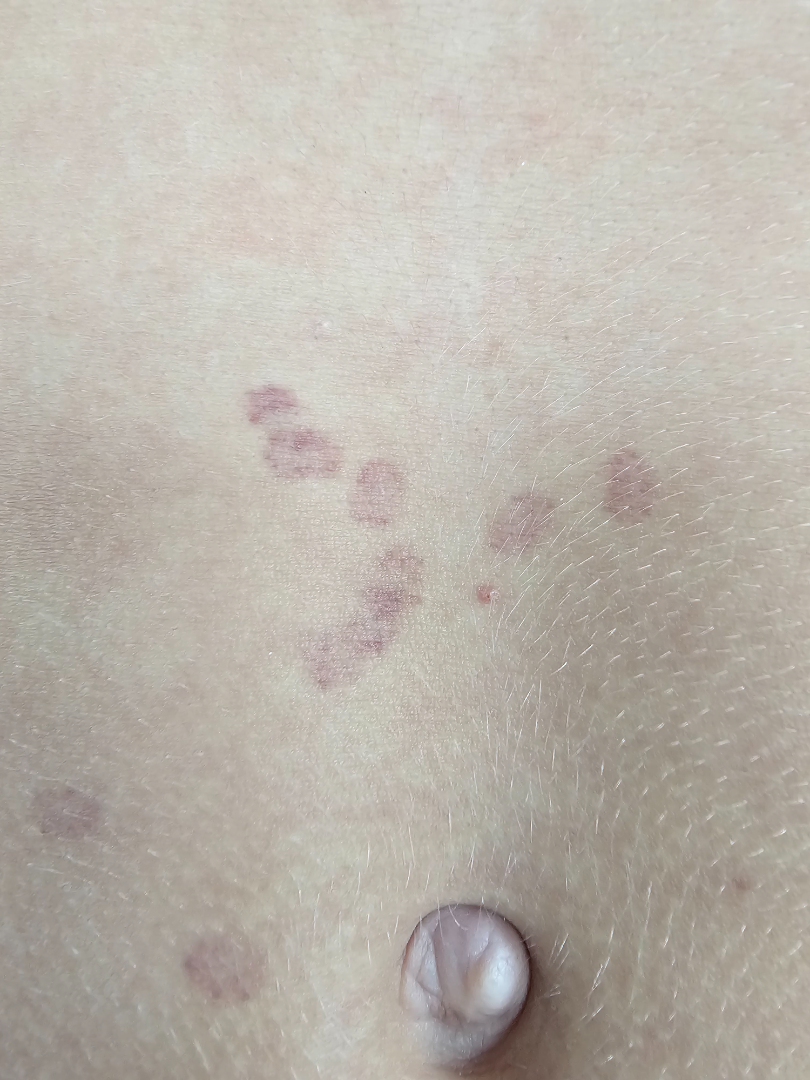assessment: not assessable.